A dermatoscopic image of a skin lesion.
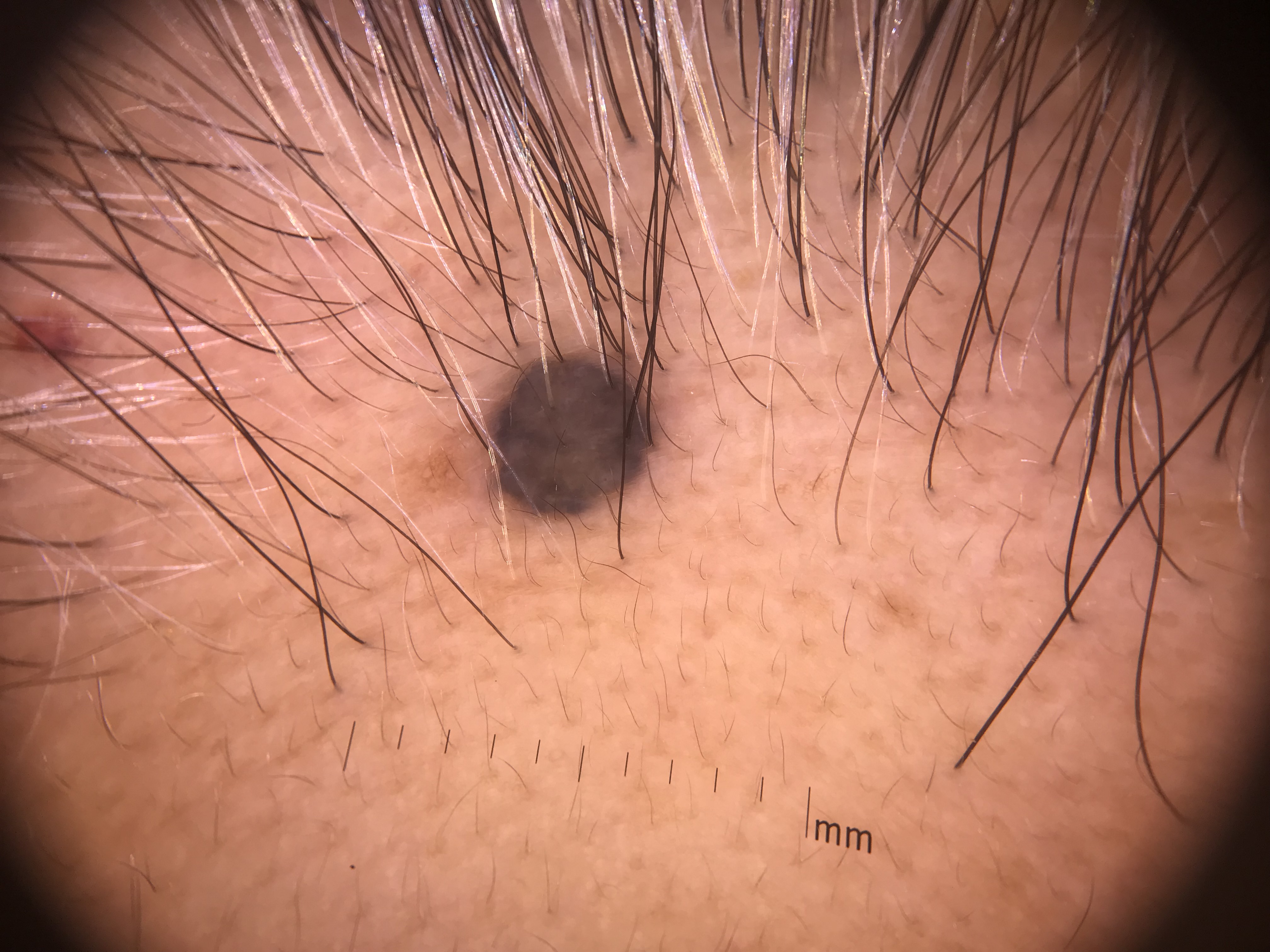<lesion>
  <diagnosis>
    <name>blue nevus</name>
    <code>bdb</code>
    <malignancy>benign</malignancy>
    <super_class>melanocytic</super_class>
    <confirmation>expert consensus</confirmation>
  </diagnosis>
</lesion>